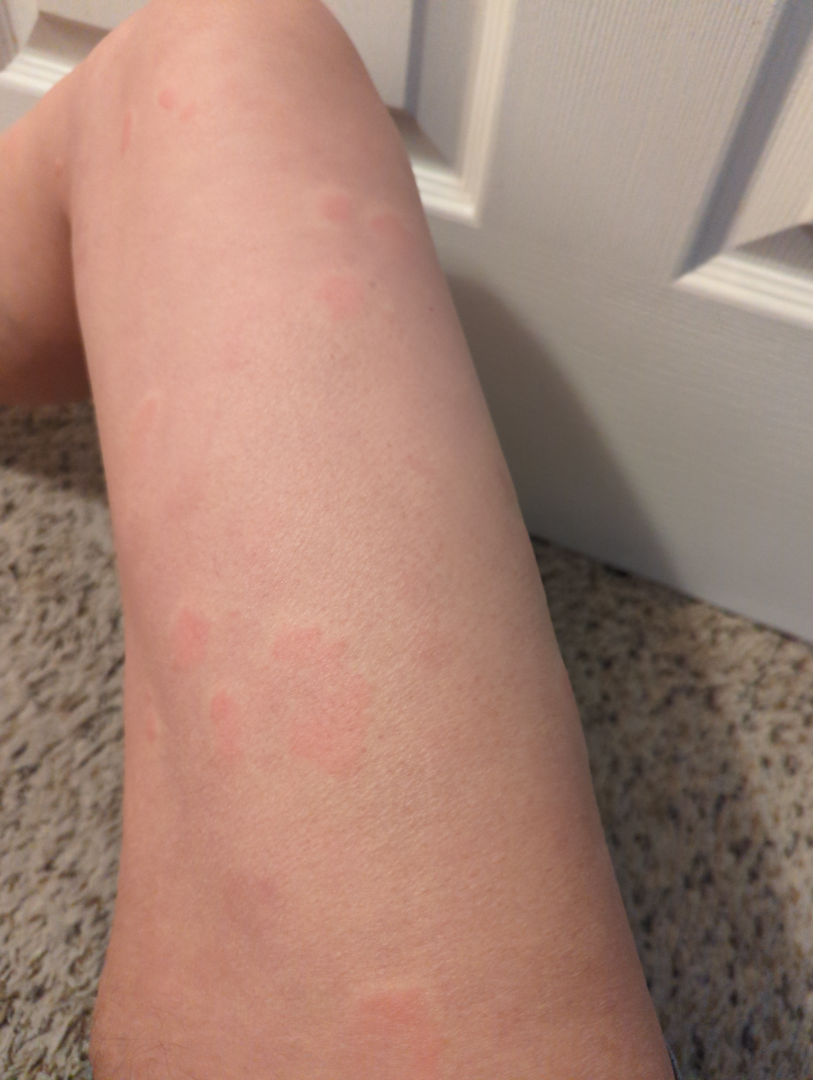Clinical context: A close-up photograph. Reported lesion symptoms include bothersome appearance. The affected area is the arm, leg and back of the hand. The contributor reports the lesion is raised or bumpy. Self-categorized by the patient as skin that appeared healthy to them. Assessment: One reviewing dermatologist: most consistent with Urticaria.